The photo was captured at an angle; female patient, age 40–49; the lesion involves the leg, back of the hand and arm: 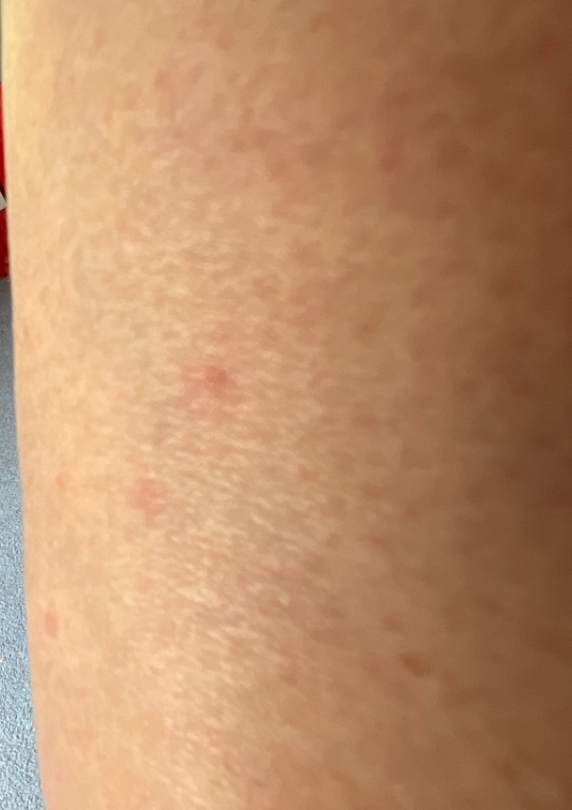On remote dermatologist review, the reviewer's impression was Folliculitis.